A female subject aged 68-72. The patient is Fitzpatrick phototype II. A dermoscopy image of a single skin lesion — 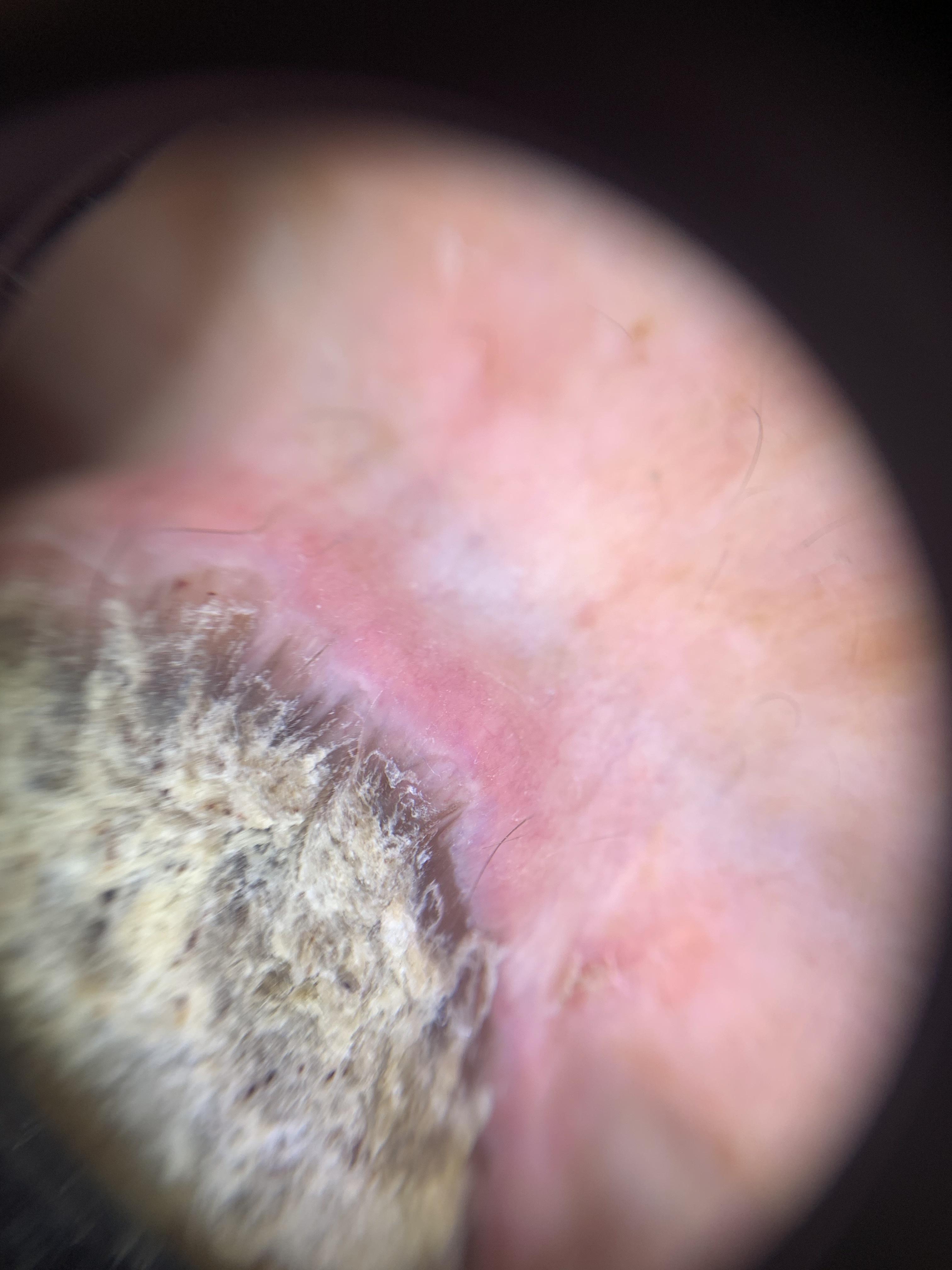body site = an upper extremity, pathology = Squamous cell carcinoma (biopsy-proven).